Dermoscopy of a skin lesion.
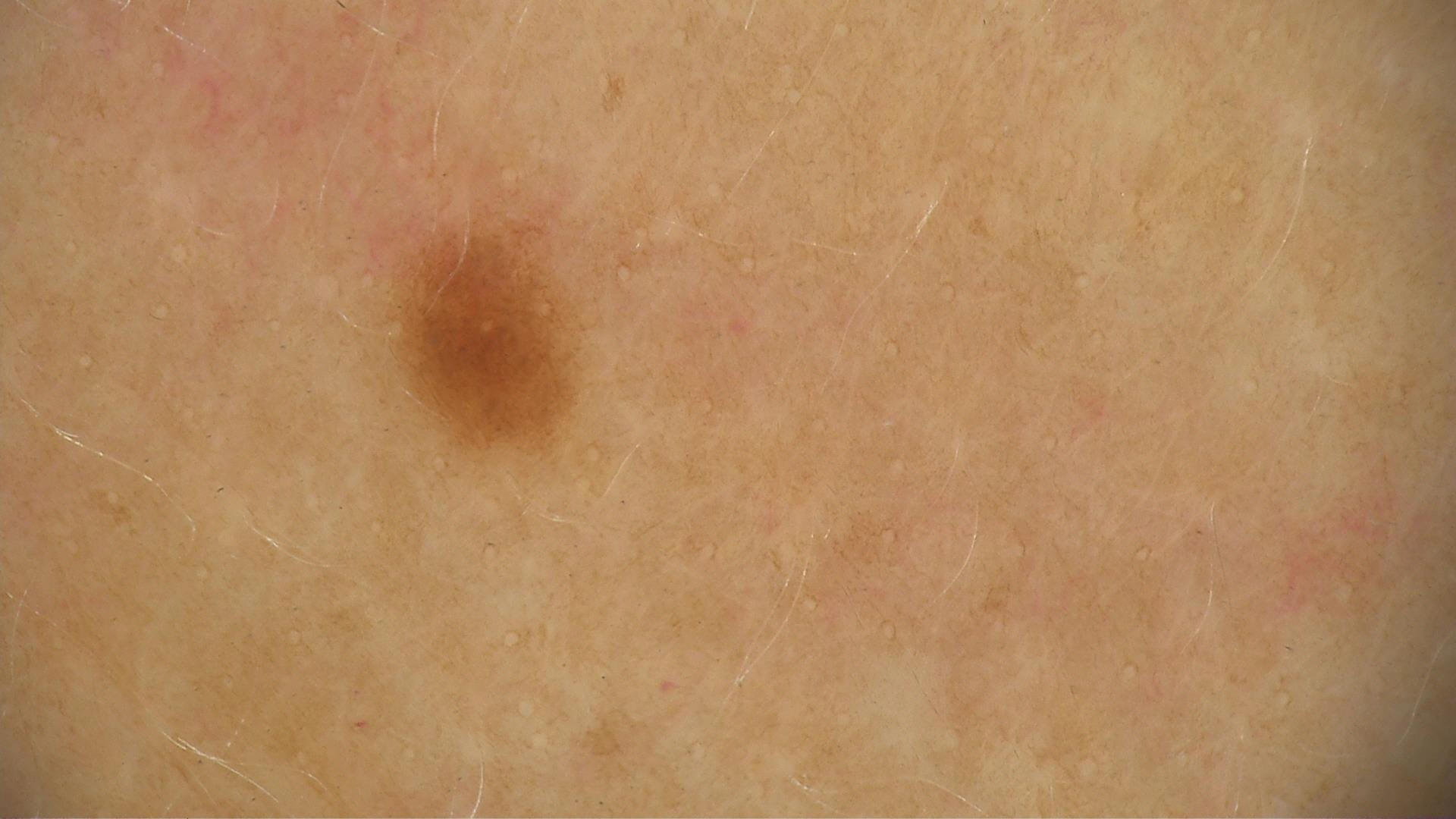<lesion>
<lesion_type>
<main_class>banal</main_class>
<pattern>junctional</pattern>
</lesion_type>
<diagnosis>
<name>junctional nevus</name>
<code>jb</code>
<malignancy>benign</malignancy>
<super_class>melanocytic</super_class>
<confirmation>expert consensus</confirmation>
</diagnosis>
</lesion>